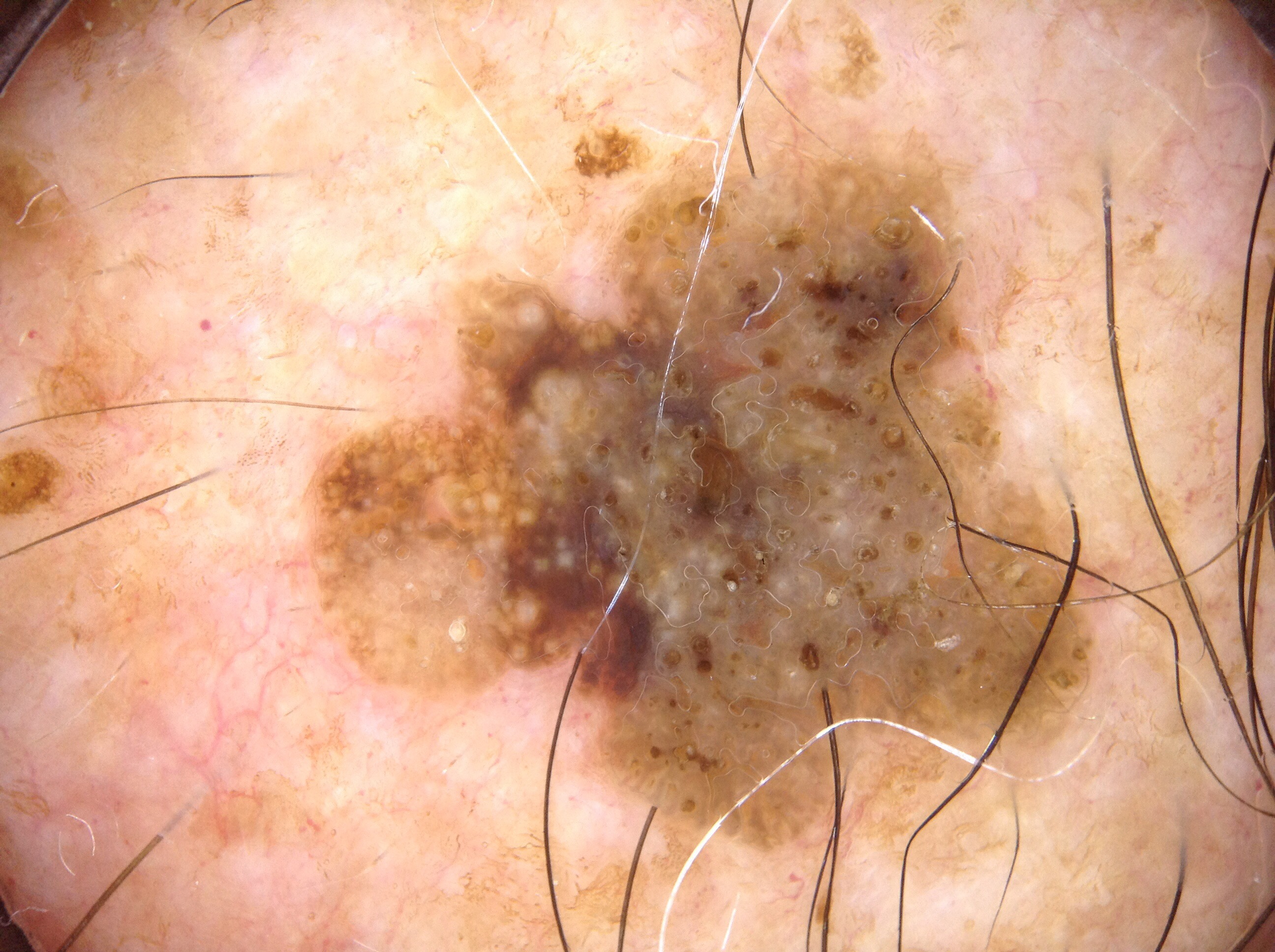A dermatoscopic image of a skin lesion. As (left, top, right, bottom), lesion location: bbox(309, 149, 1095, 847). Clinically diagnosed as a seborrheic keratosis, a benign lesion.